A skin lesion imaged with contact-polarized dermoscopy · a female subject in their 80s.
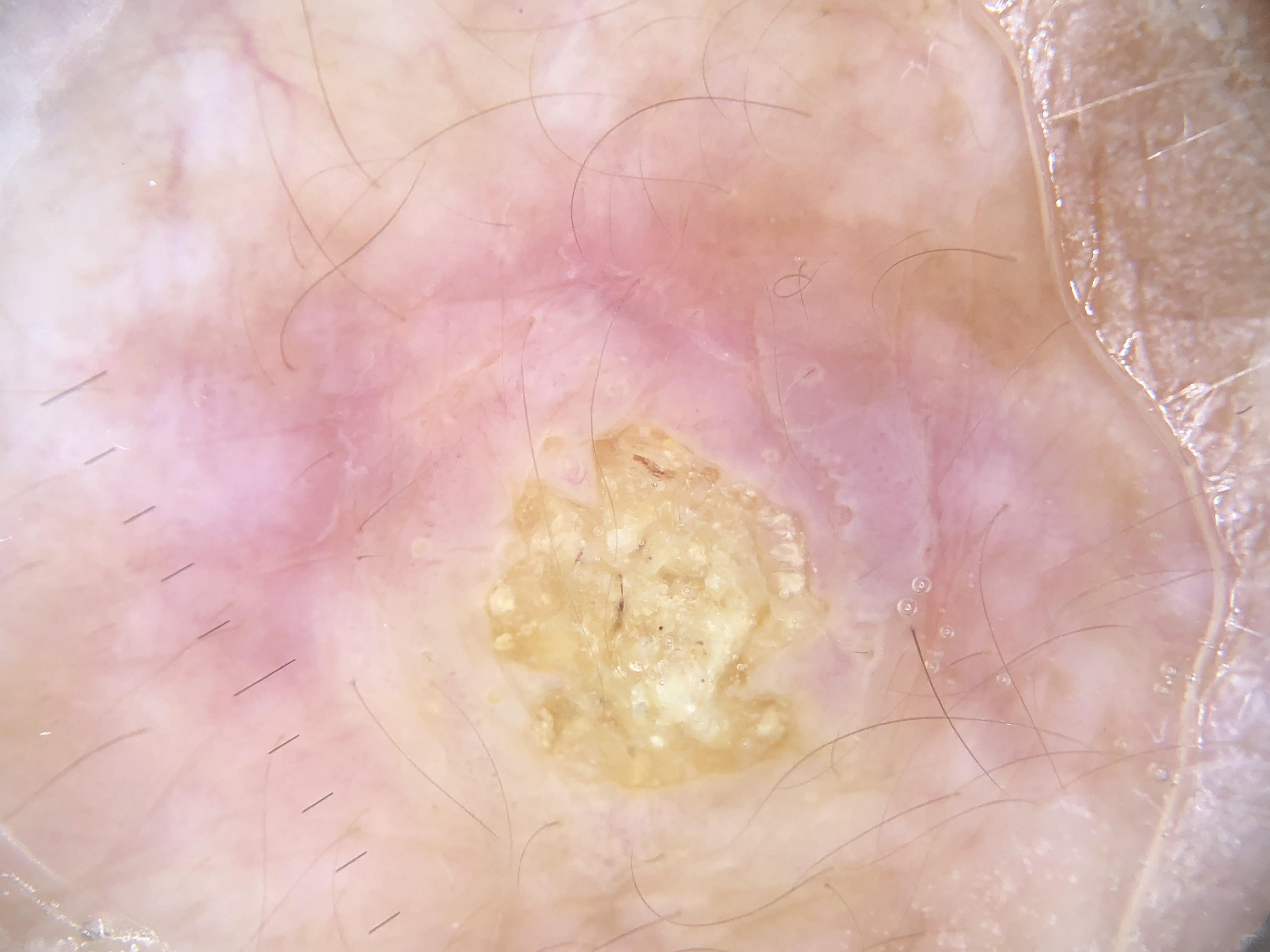Findings:
• site — a lower extremity
• diagnostic label — Squamous cell carcinoma (biopsy-proven)